Collected as part of a research study, without a referral diagnosis · a male patient 72 years old — 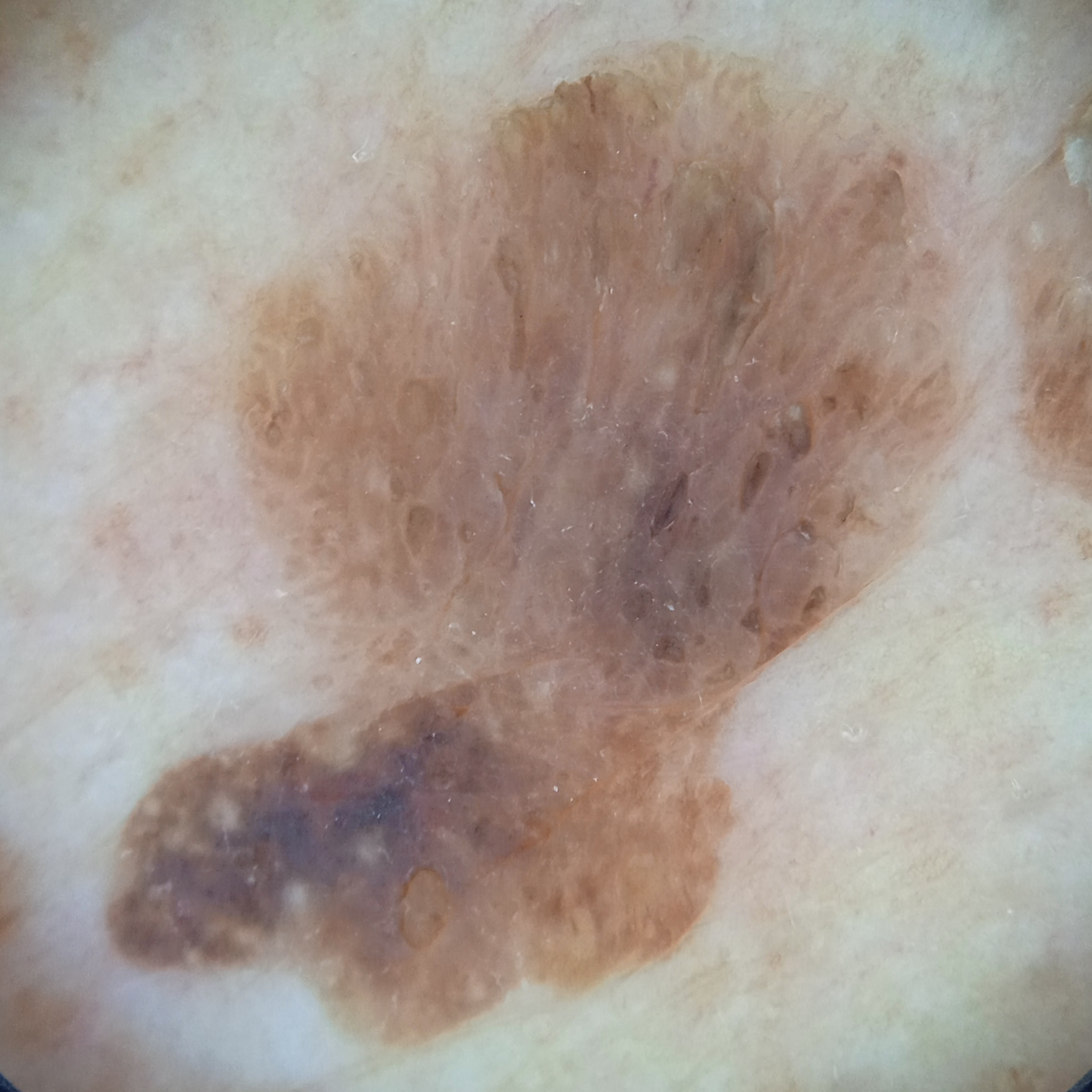Findings: The lesion is on the back. Assessment: Reviewed by four dermatologists, the consensus diagnosis was a seborrheic keratosis; agreement among the reviewers was unanimous; the reviewers were highly confident.